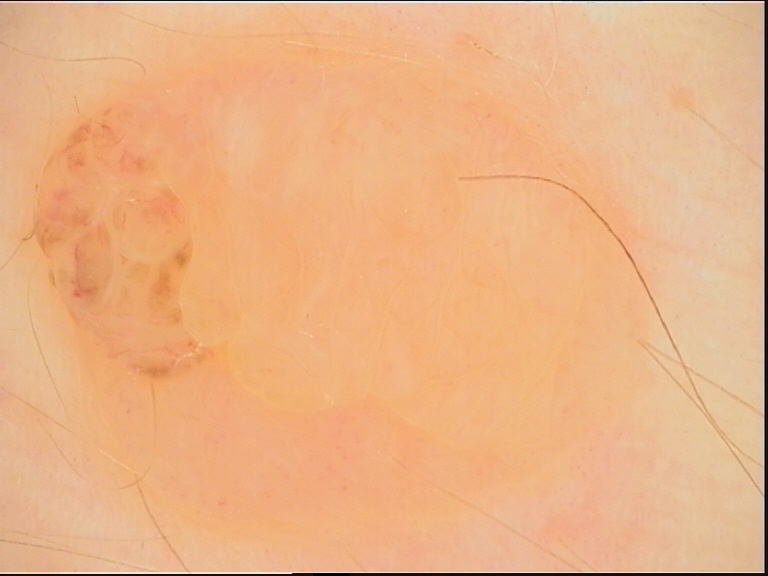imaging = dermatoscopy; classification = banal; diagnostic label = dermal nevus (expert consensus).